A skin lesion imaged with a dermatoscope: 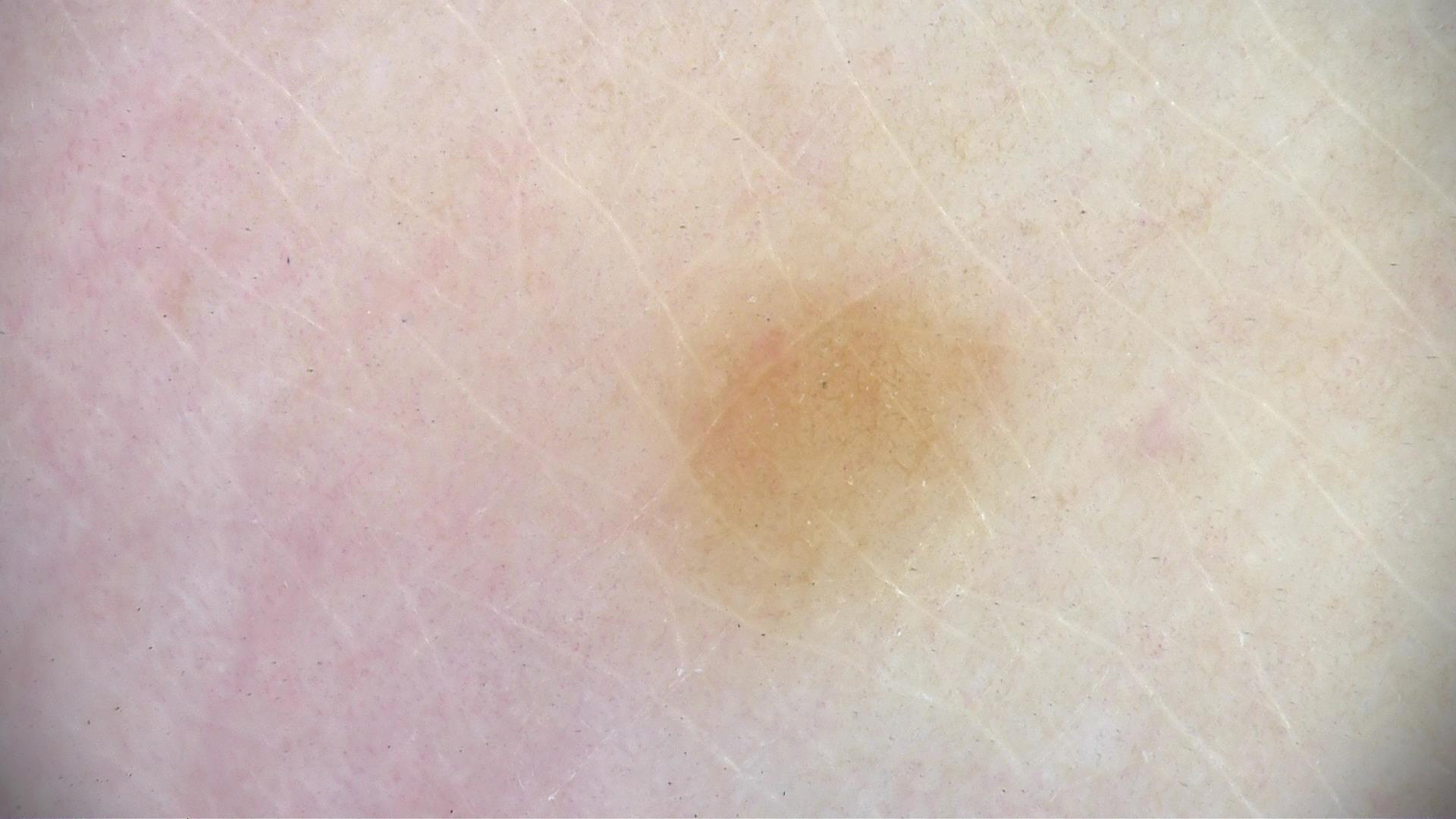  lesion_type:
    main_class: banal
    pattern: dermal
  diagnosis:
    name: dermal nevus
    code: db
    malignancy: benign
    super_class: melanocytic
    confirmation: expert consensus